A female subject age 54 · collected as part of a research study, without a referral diagnosis · numerous moles by the patient's own estimate · by self-report, a family history of skin cancer, a personal history of skin cancer, and a personal history of cancer · the patient says their skin reddens with sun exposure: 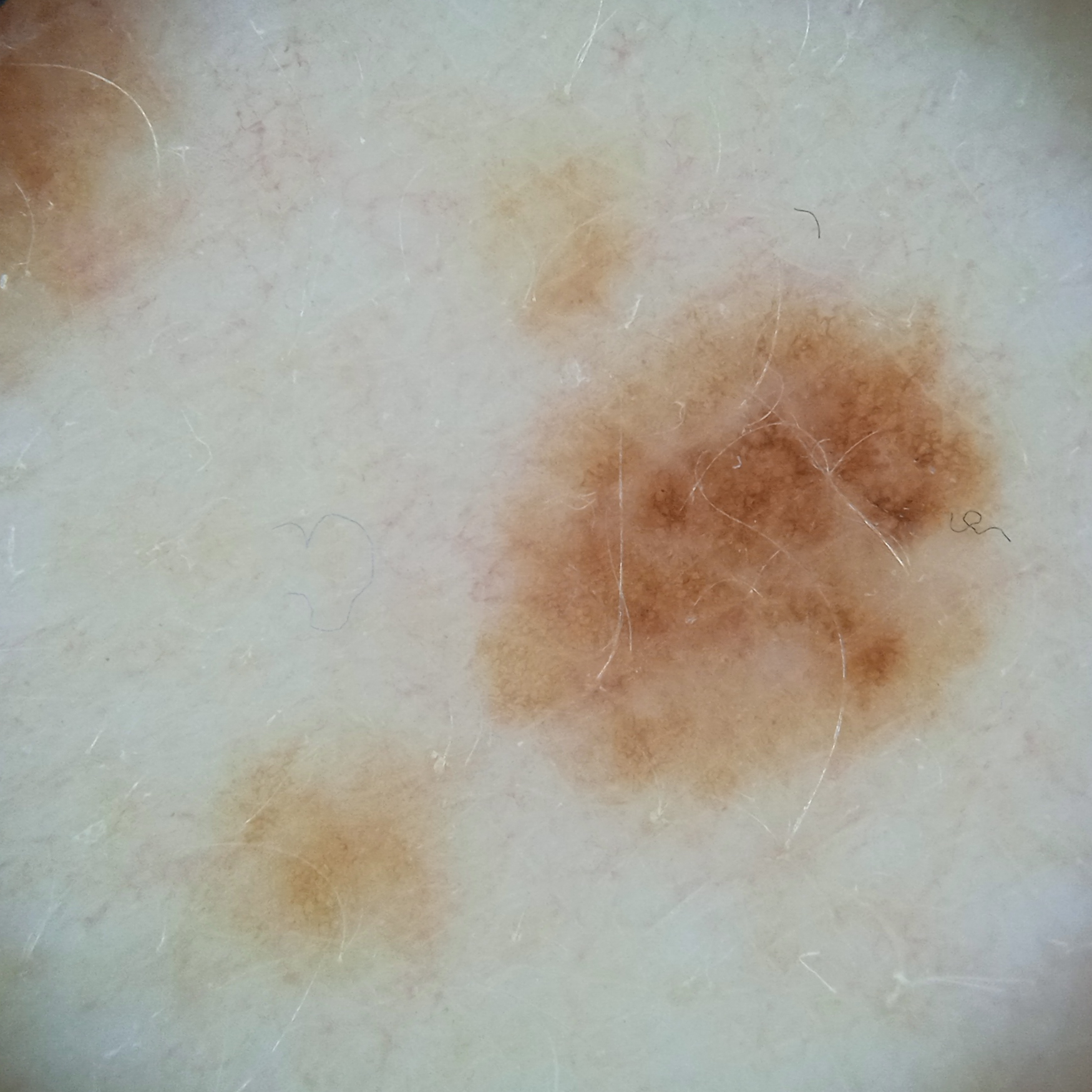location = the back; lesion size = 6.4 mm; diagnosis = atypical (dysplastic) nevus — dermatologist consensus.